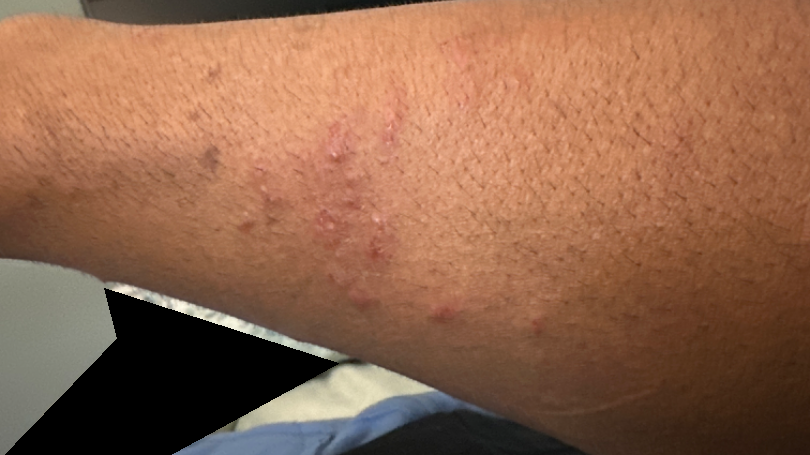The reviewing dermatologists' impression was: favoring Folliculitis; also raised was Allergic Contact Dermatitis; less likely is Localized skin infection.